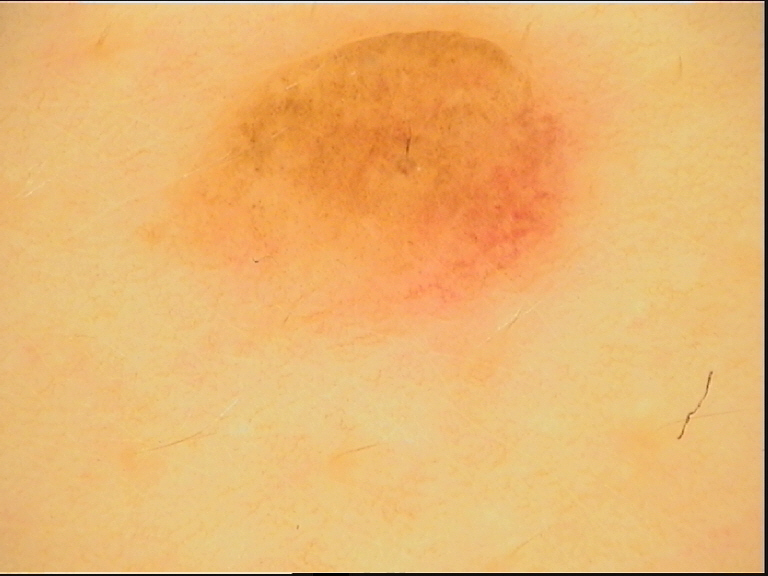A dermatoscopic image of a skin lesion. The morphology is that of a banal lesion. Labeled as a dermal nevus.